Located on the leg; an image taken at an angle; male contributor, age 18–29.
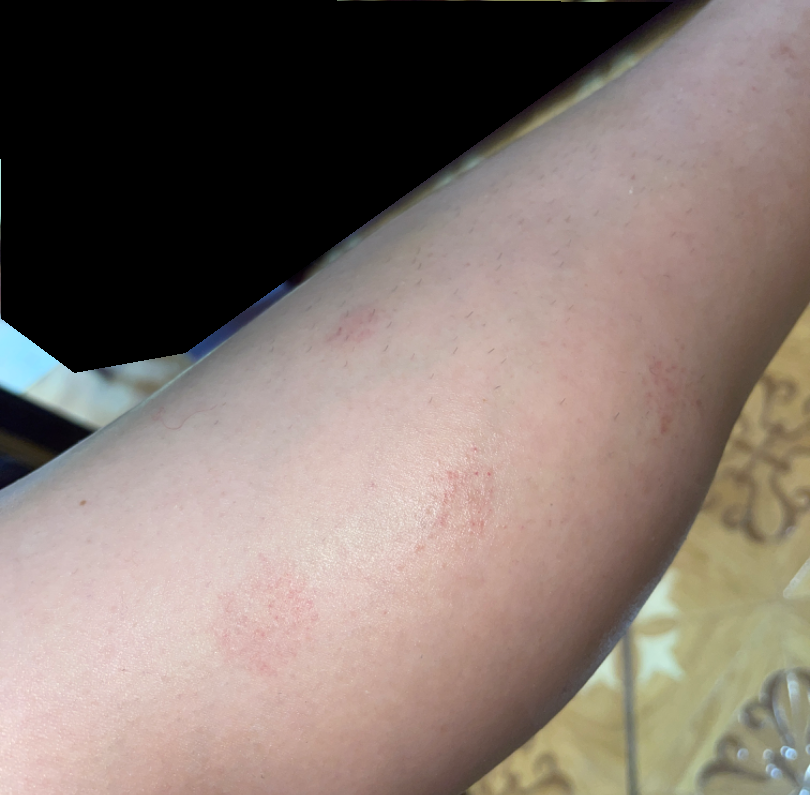– assessment · three dermatologists each reviewed the case: the leading impression is Eczema; less likely is Pigmented purpuric eruption